This image was taken at a distance; the subject is a male aged 18–29; the arm is involved:
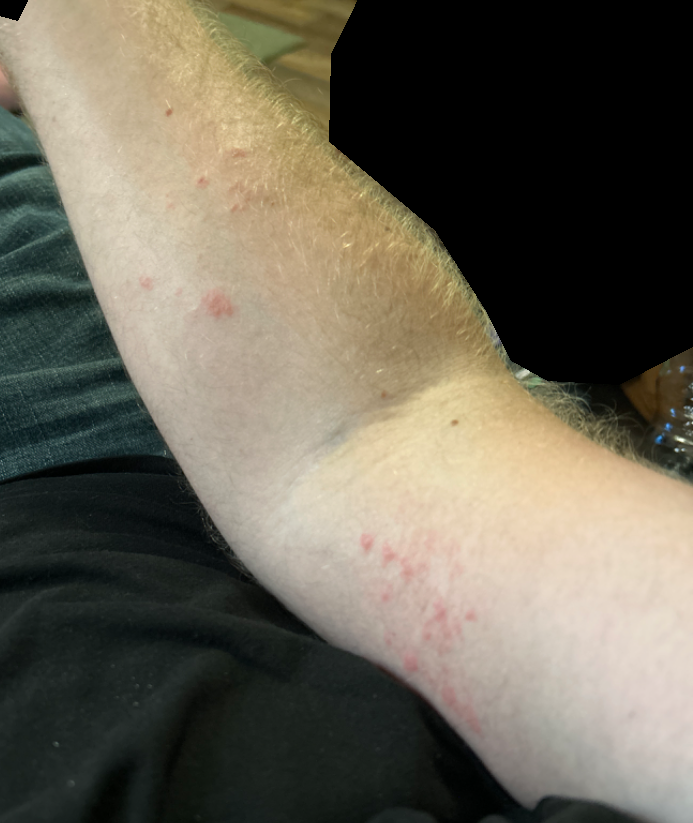Q: Could the case be diagnosed?
A: indeterminate from the photograph
Q: What is the lesion texture?
A: raised or bumpy and fluid-filled
Q: Reported symptoms?
A: pain, itching, burning, enlargement and bothersome appearance
Q: How does the patient describe it?
A: a rash
Q: Duration?
A: less than one week